The patient considered this a rash. The lesion is described as flat. The affected area is the leg. The photograph is a close-up of the affected area.
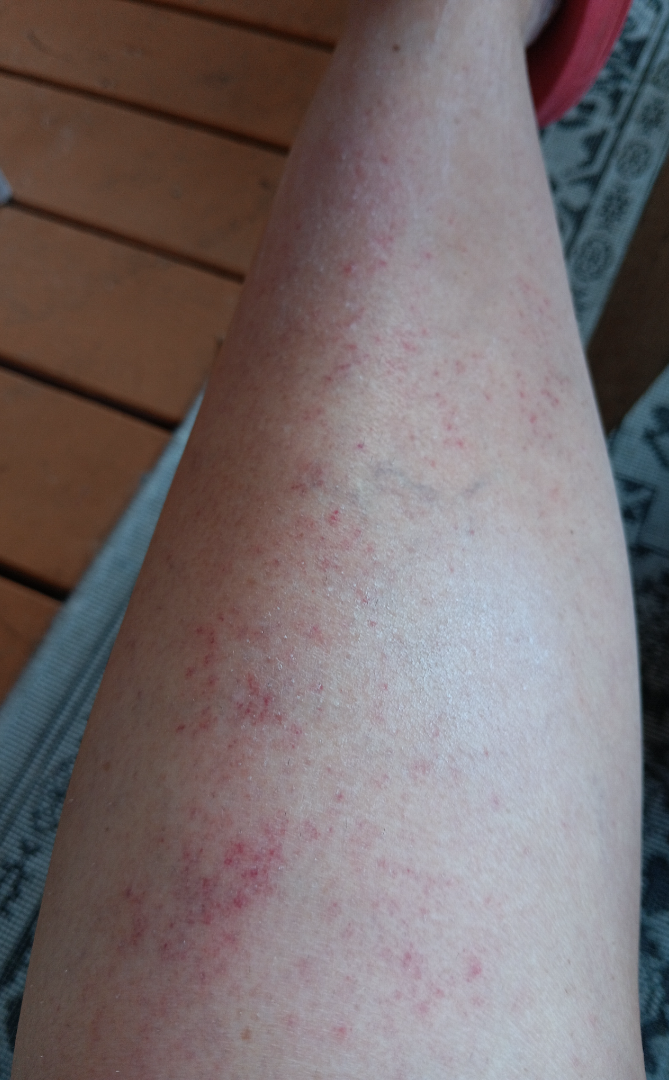{"differential": {"tied_lead": ["Pigmented purpuric eruption", "Eczema", "Leukocytoclastic Vasculitis"]}}